This is a dermoscopic photograph of a skin lesion · the patient is a female approximately 60 years of age: 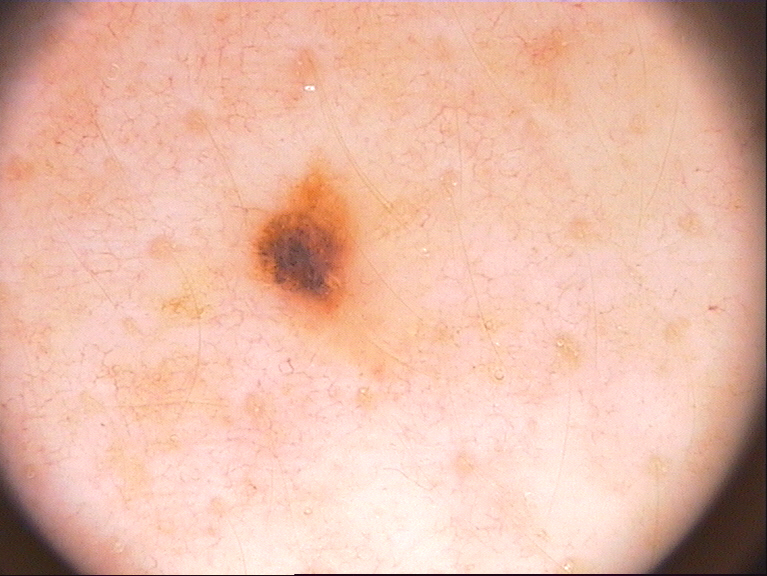Dermoscopy demonstrates no streaks, negative network, pigment network, milia-like cysts, or globules. In (x1, y1, x2, y2) order, the lesion is located at 247 161 365 329. The diagnostic assessment was a melanocytic nevus.